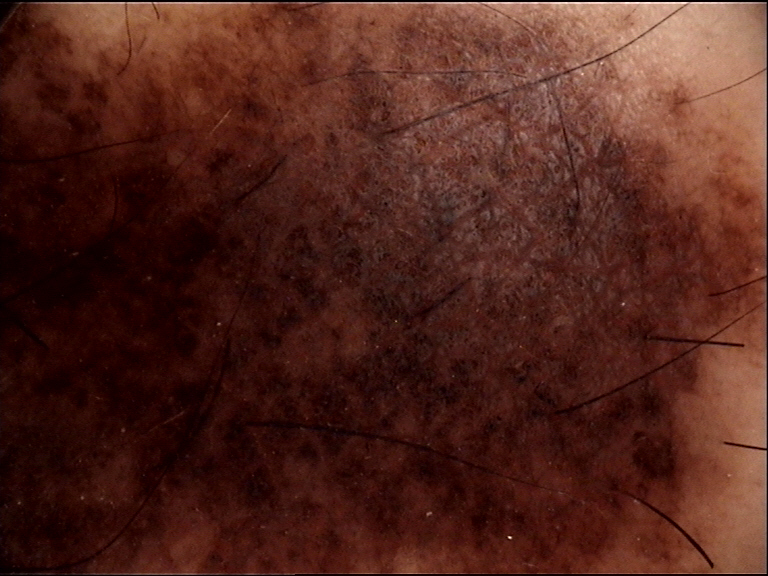Impression: Labeled as a congenital compound nevus.